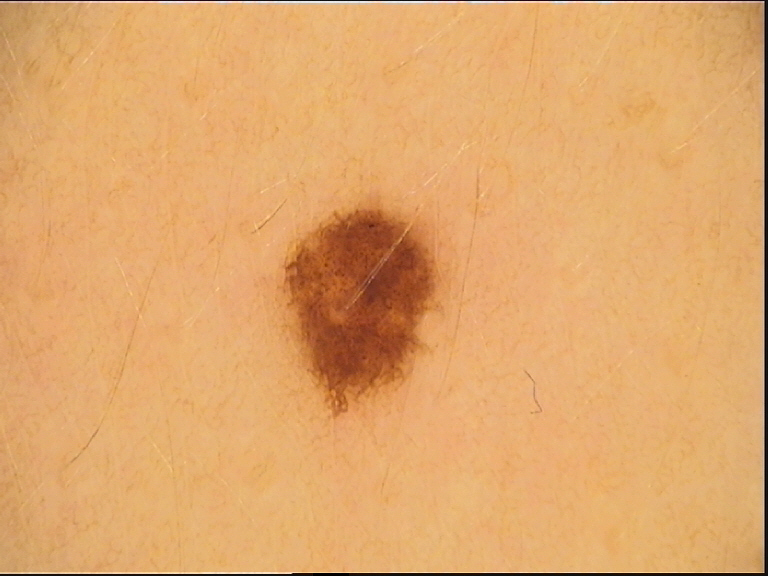A skin lesion imaged with a dermatoscope.
Labeled as a dysplastic junctional nevus.